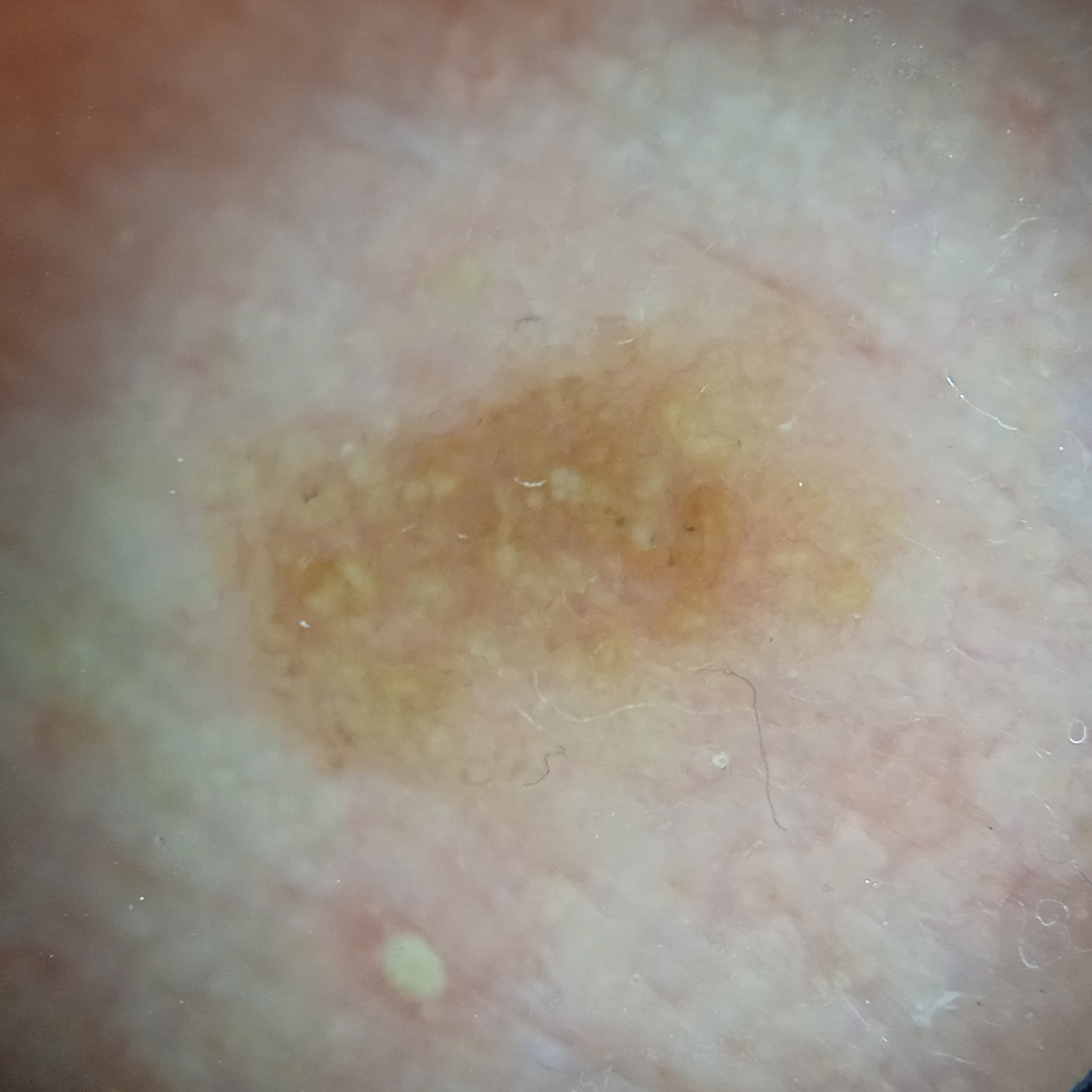Q: What was the diagnosis?
A: actinic keratosis (dermatologist consensus)